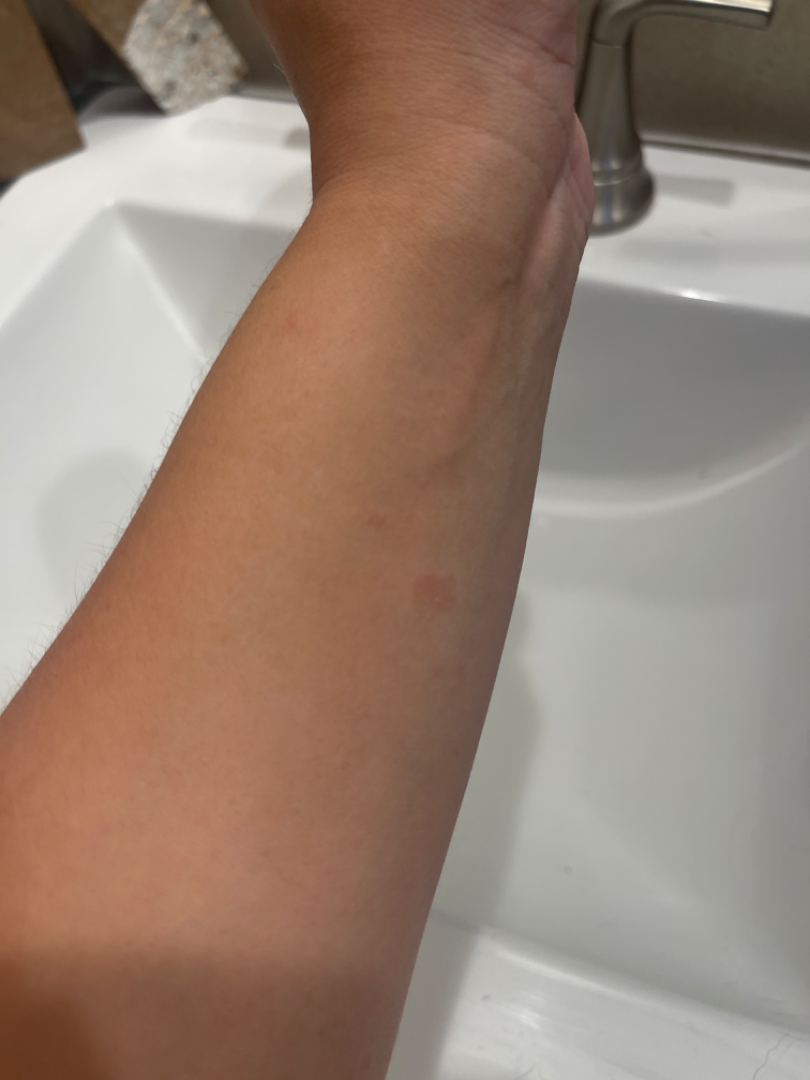– assessment · unable to determine
– site · arm
– photo taken · at an angle
– patient · female, age 18–29